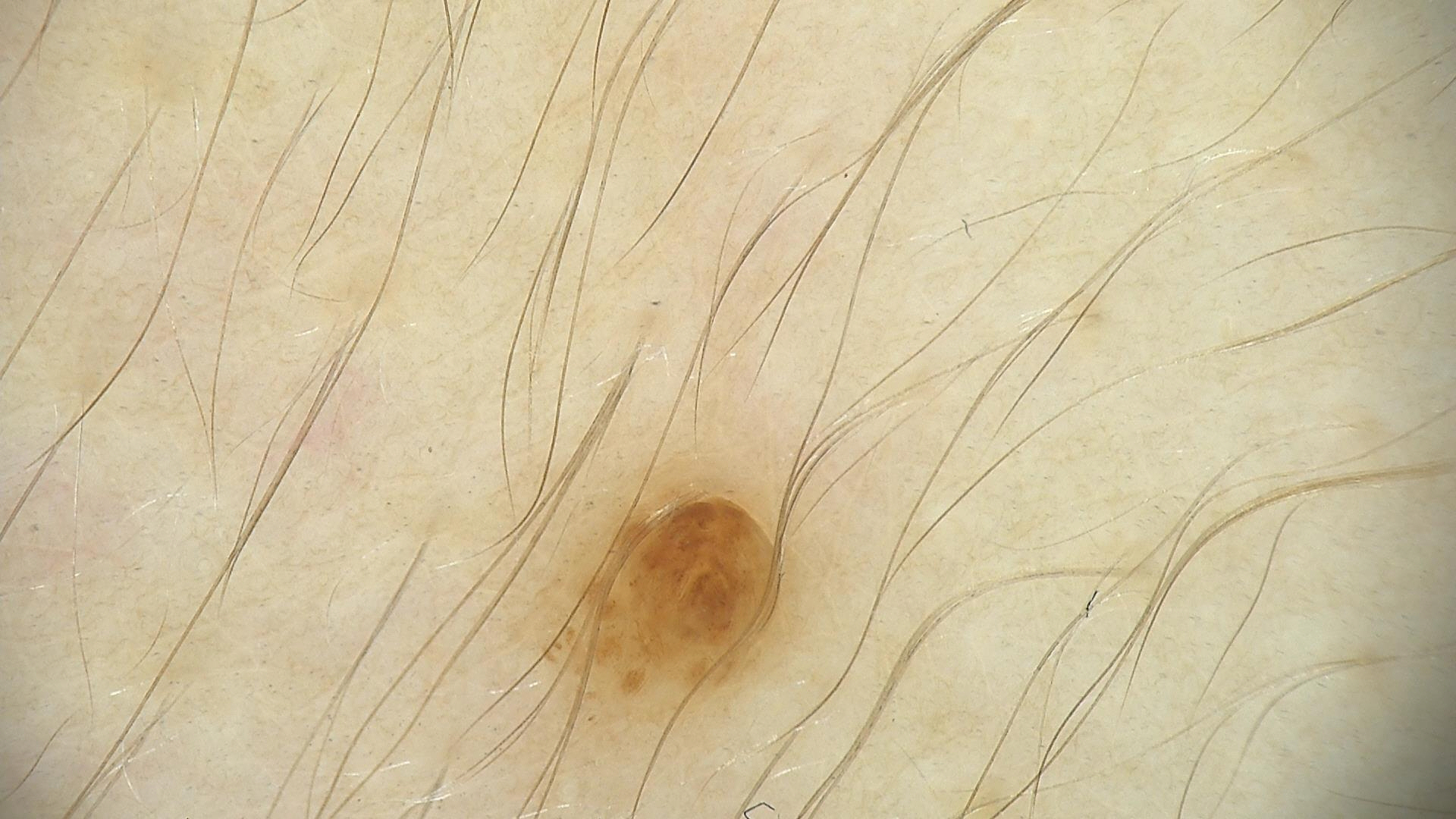A dermoscopy image of a single skin lesion. The architecture is that of a banal lesion. Diagnosed as a compound nevus.